The photograph is a close-up of the affected area.
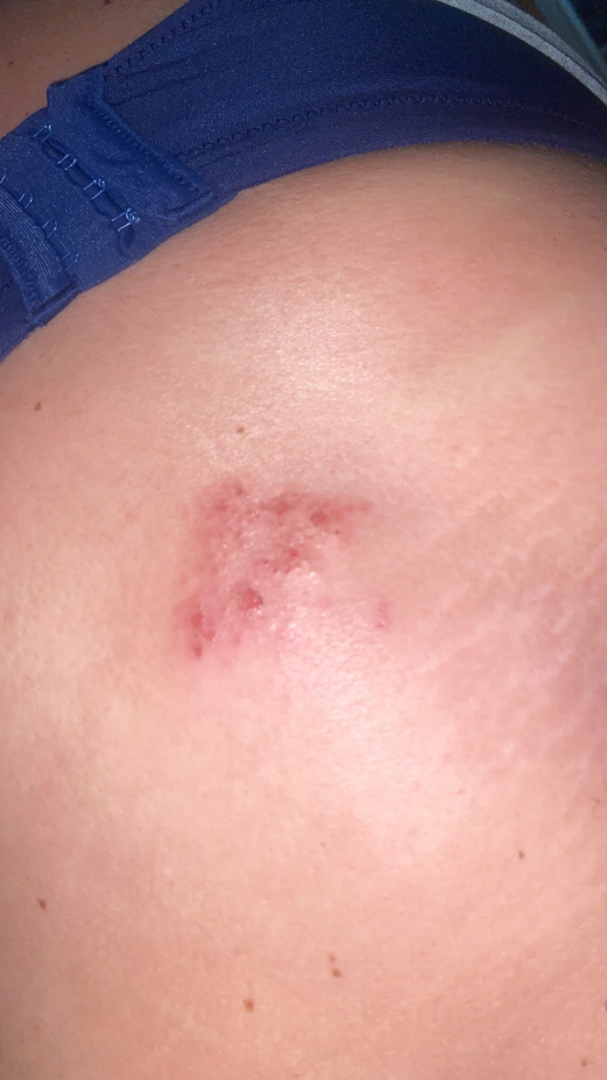Skin tone: FST IV. Reviewed remotely by one dermatologist: the leading impression is Allergic Contact Dermatitis; an alternative is Irritant Contact Dermatitis.